Close-up view. The leg, arm, head or neck and back of the torso are involved. Female subject, age 18–29.
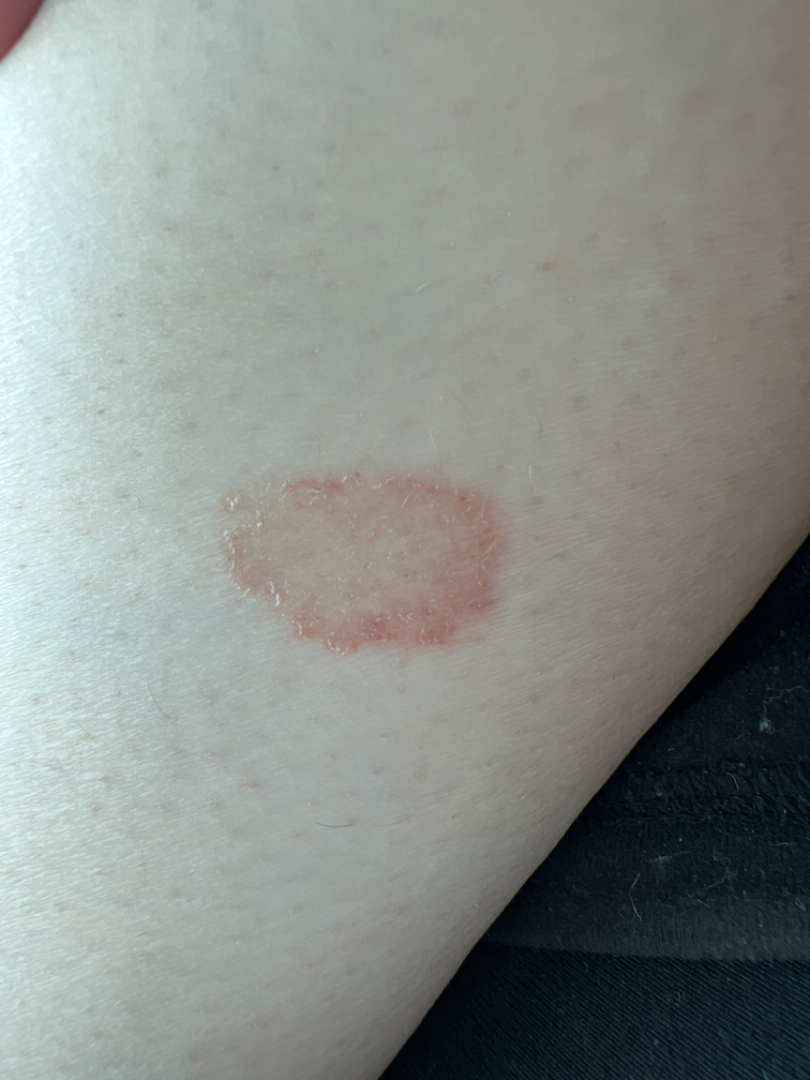<summary>
  <texture>flat</texture>
  <systemic_symptoms>none reported</systemic_symptoms>
  <symptoms>itching</symptoms>
  <duration>one to three months</duration>
  <differential>
    <tied_lead>Eczema, Tinea</tied_lead>
    <considered>Porokeratosis</considered>
    <unlikely>Granuloma annulare</unlikely>
  </differential>
</summary>